A clinical close-up photograph of a skin lesion. A female patient in their late 50s — 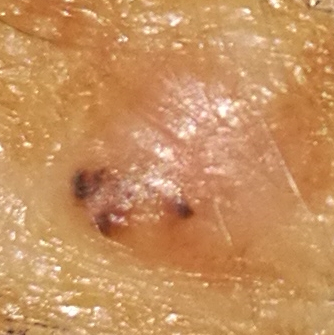The lesion is located on a forearm.
Per patient report, the lesion itches, has bled, and is elevated, but does not hurt.
Biopsy-confirmed as a basal cell carcinoma.